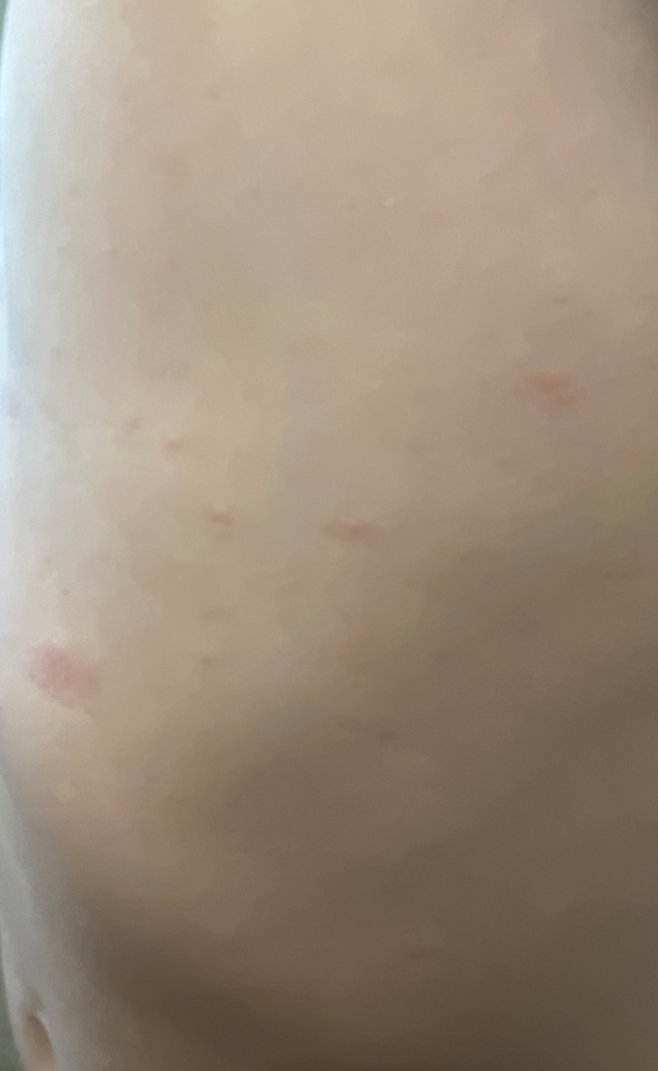Patient information:
The photo was captured at an angle.
Review:
Favoring Pityriasis rosea; the differential also includes Eczema; also raised was Syphilis.